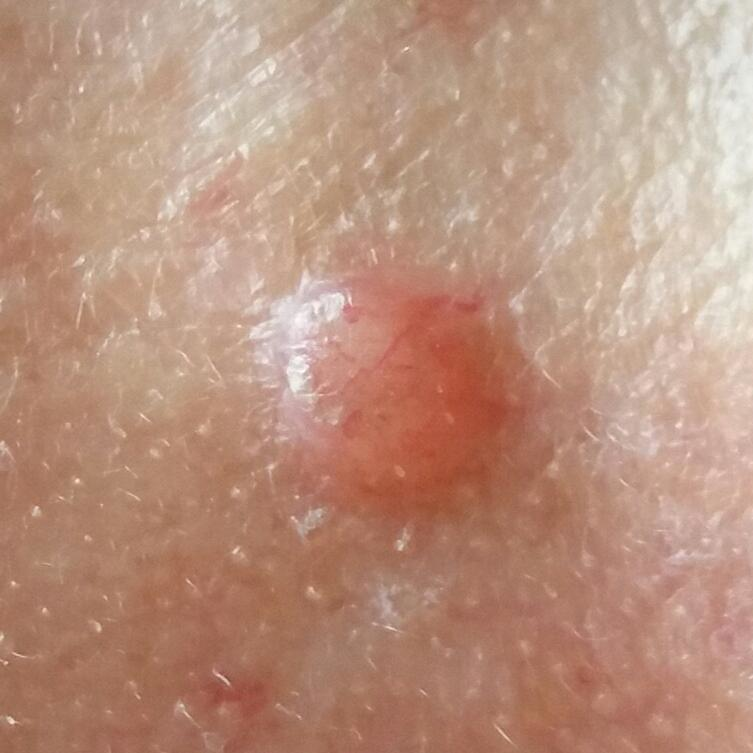pathology: basal cell carcinoma (biopsy-proven).